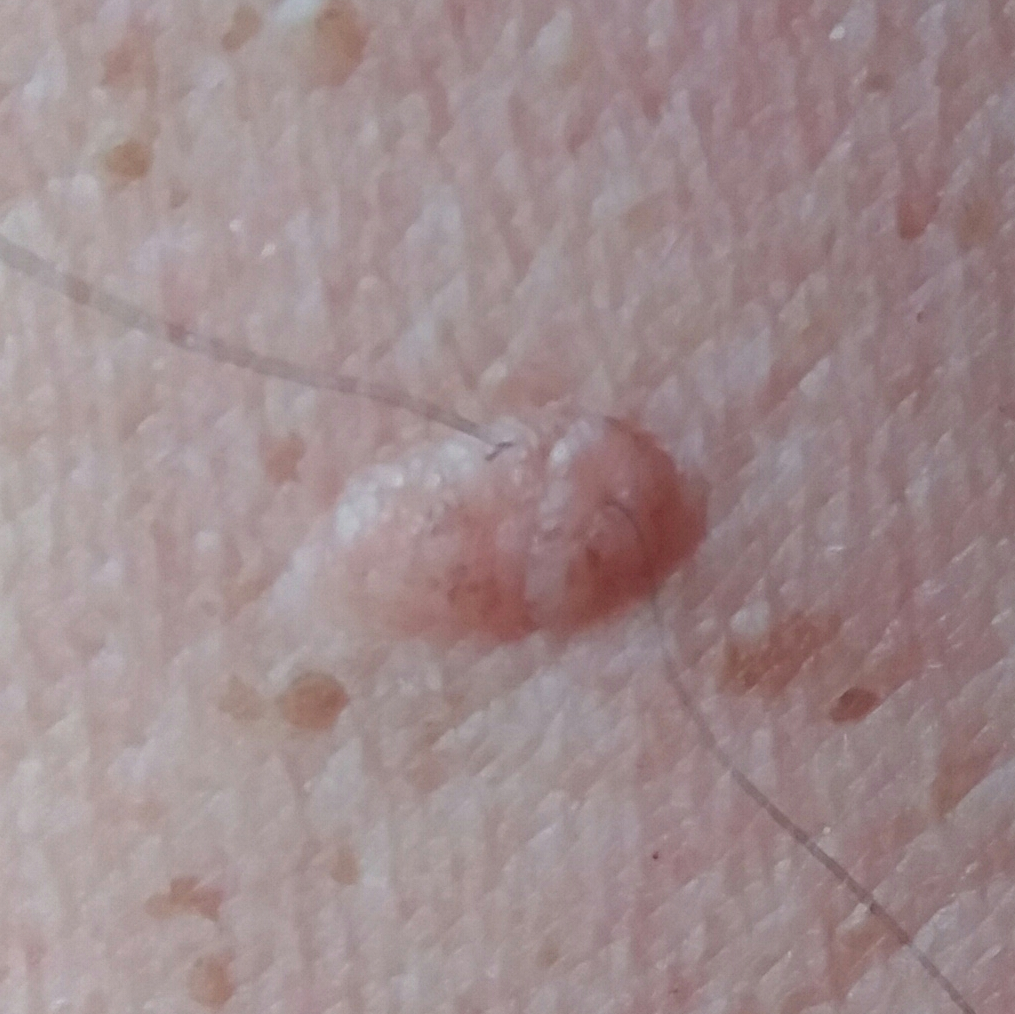<skin_lesion>
  <image>smartphone clinical photo</image>
  <lesion_location>a thigh</lesion_location>
  <symptoms>
    <present>elevation</present>
    <absent>bleeding, itching</absent>
  </symptoms>
  <diagnosis>
    <name>nevus</name>
    <code>NEV</code>
    <malignancy>benign</malignancy>
    <confirmation>clinical consensus</confirmation>
  </diagnosis>
</skin_lesion>